The patient is 18–29, female; the photograph is a close-up of the affected area; located on the leg — 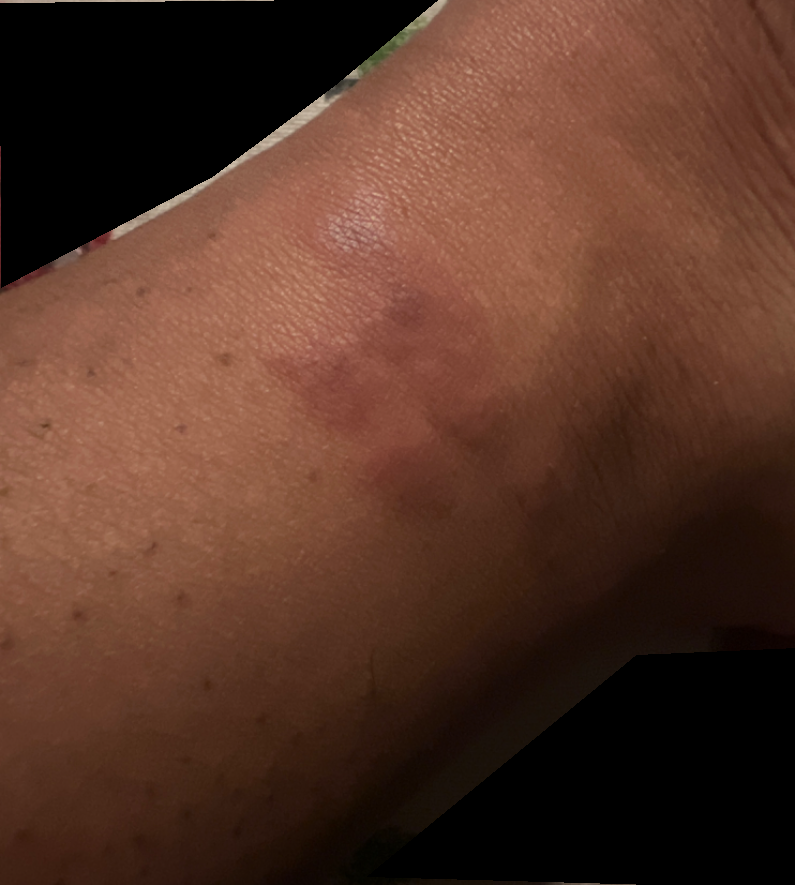No relevant systemic symptoms. Texture is reported as raised or bumpy and flat. Symptoms reported: itching. Allergic Contact Dermatitis (most likely); Insect Bite (possible); Eczema (unlikely).